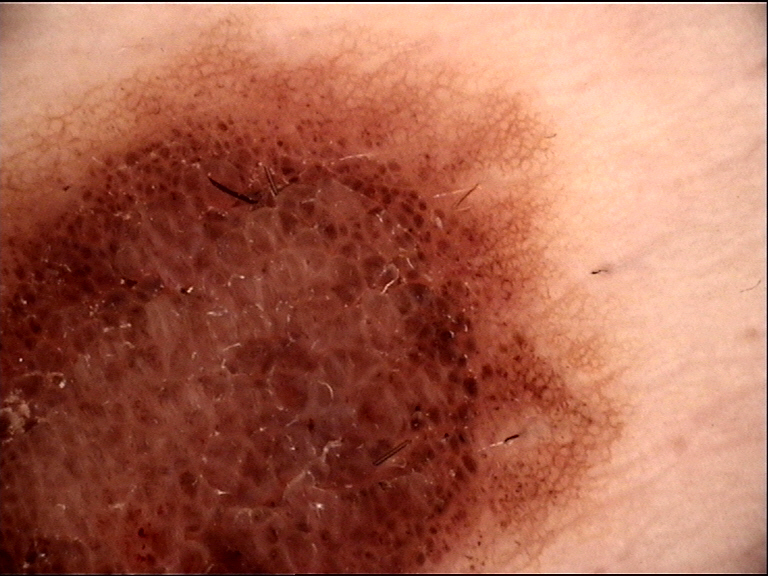Findings:
* modality · dermatoscopy
* diagnostic label · compound nevus (expert consensus)